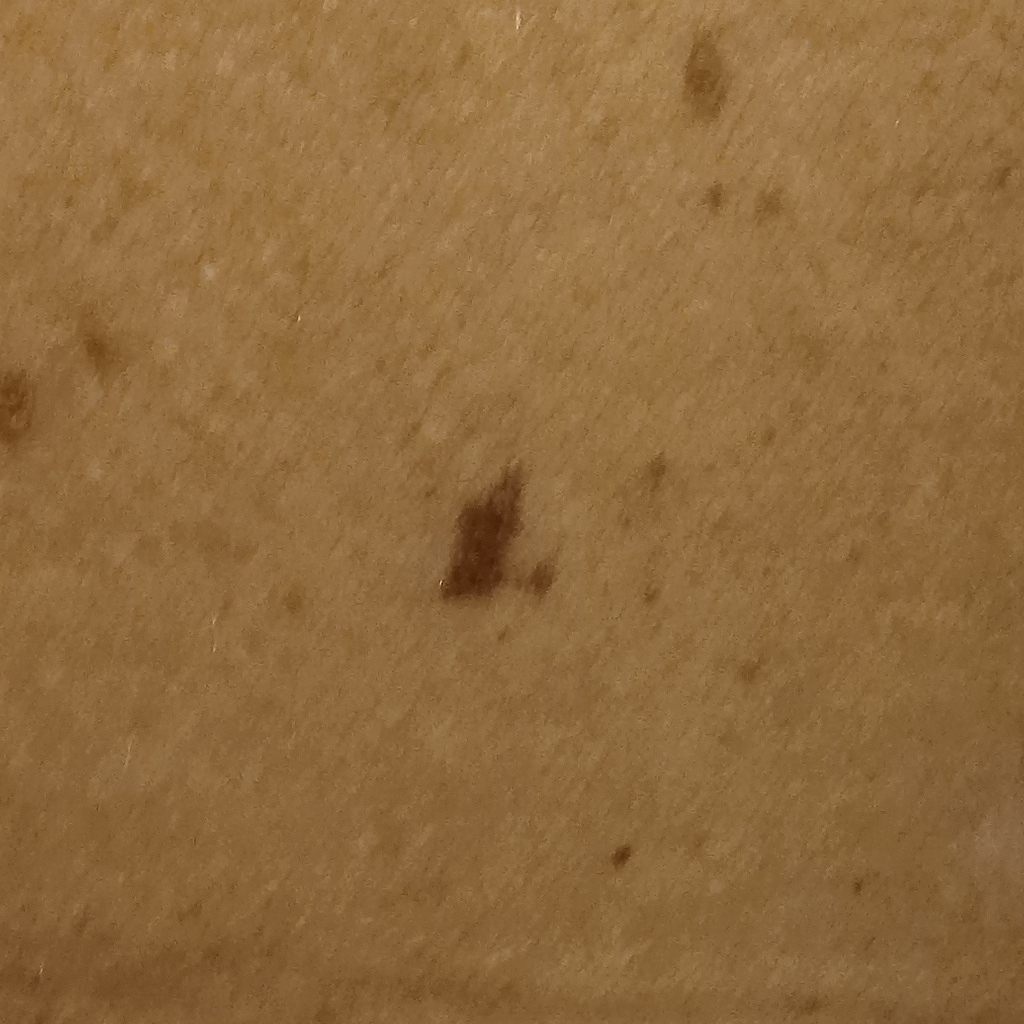Histopathologically confirmed as an atypical (dysplastic) nevus, following excision.